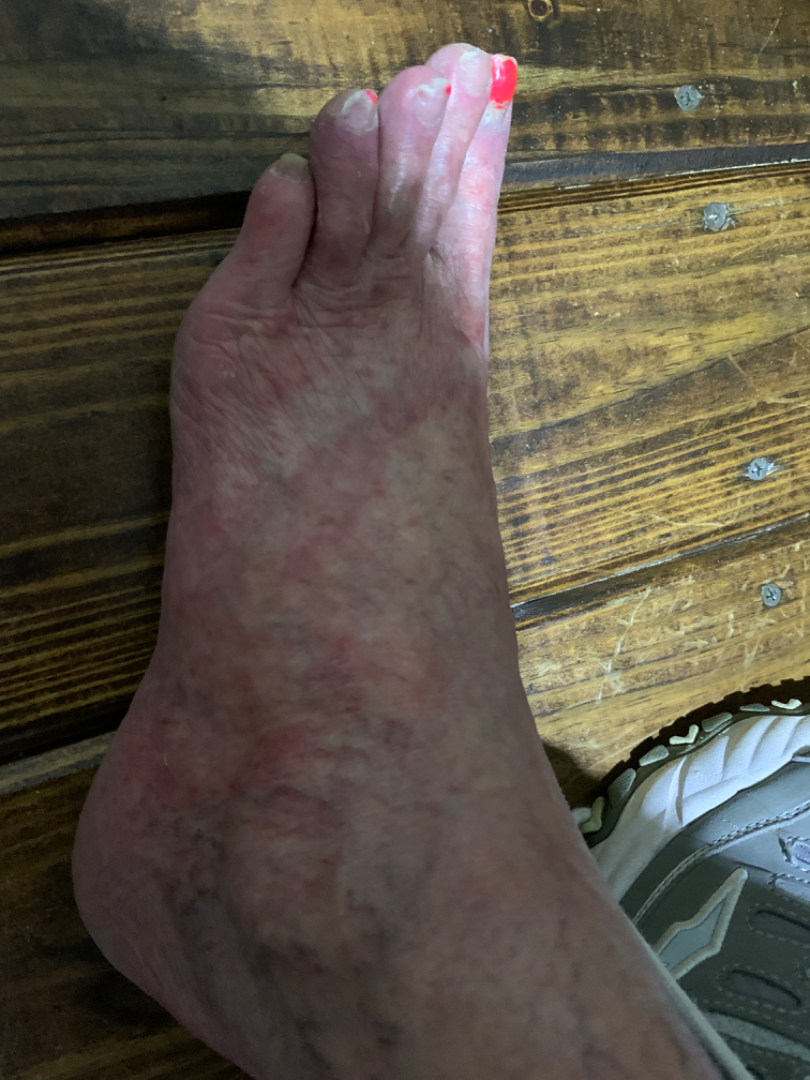Background: The photo was captured at an angle. The patient is female. Symptoms reported: itching and bothersome appearance. Reported duration is one to four weeks. The lesion involves the top or side of the foot. Findings: On teledermatology review, most consistent with Tinea.